Dermoscopy of a skin lesion: 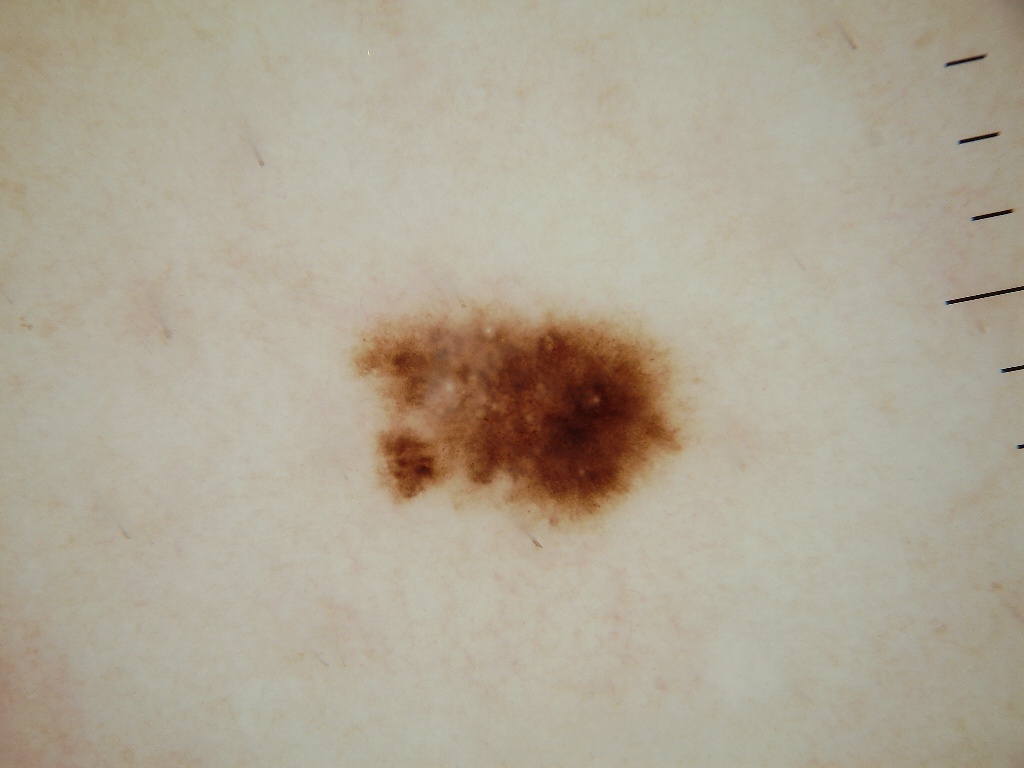  dermoscopic_features:
    present:
      - globules
      - milia-like cysts
    absent:
      - streaks
      - negative network
      - pigment network
  lesion_location:
    bbox_xyxy:
      - 348
      - 297
      - 693
      - 536
  diagnosis:
    name: melanoma
    malignancy: malignant
    lineage: melanocytic
    provenance: histopathology